A skin lesion imaged with a dermatoscope.
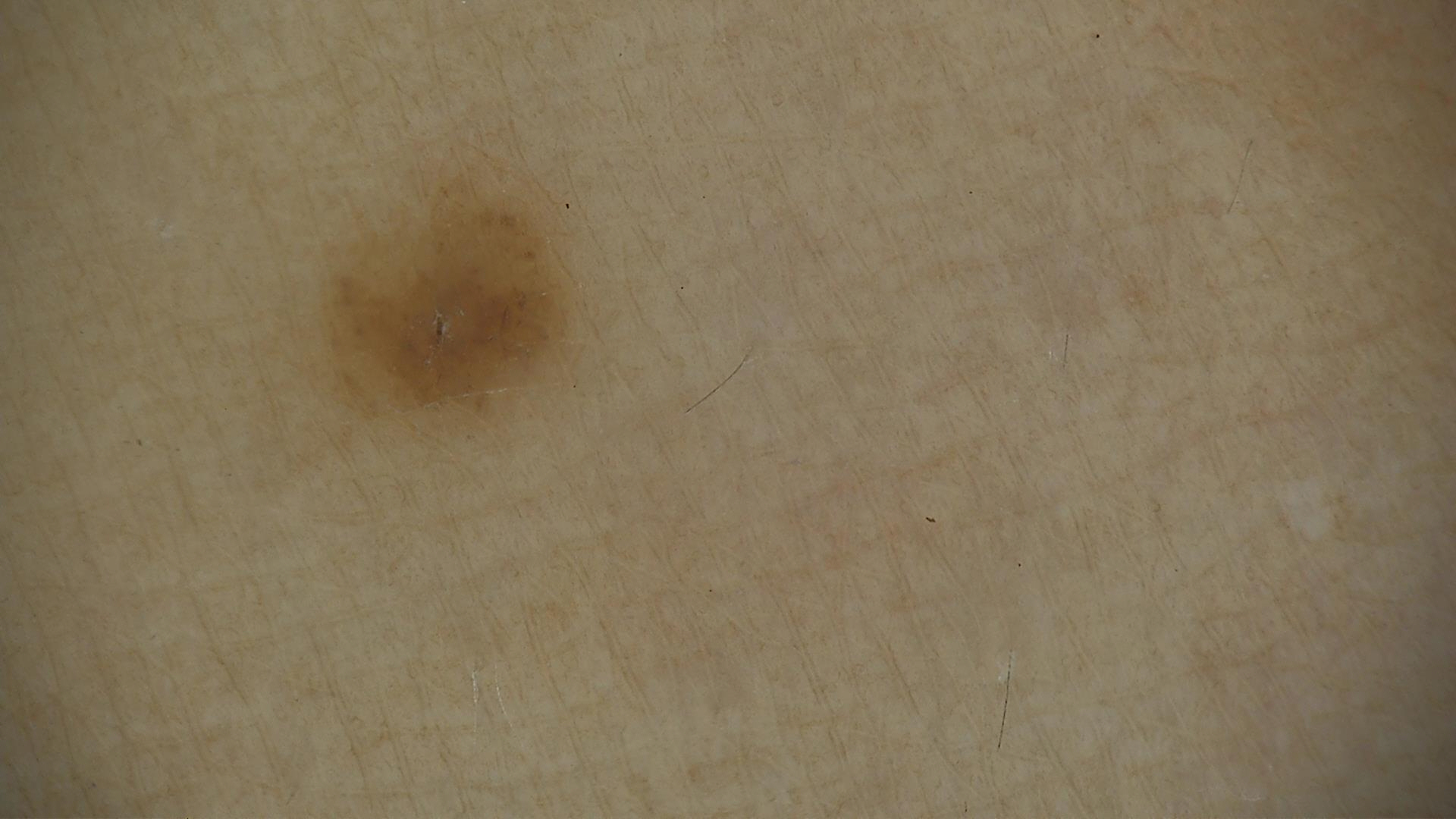The diagnostic label was a benign lesion — a dysplastic junctional nevus.